A skin lesion imaged with a dermatoscope — 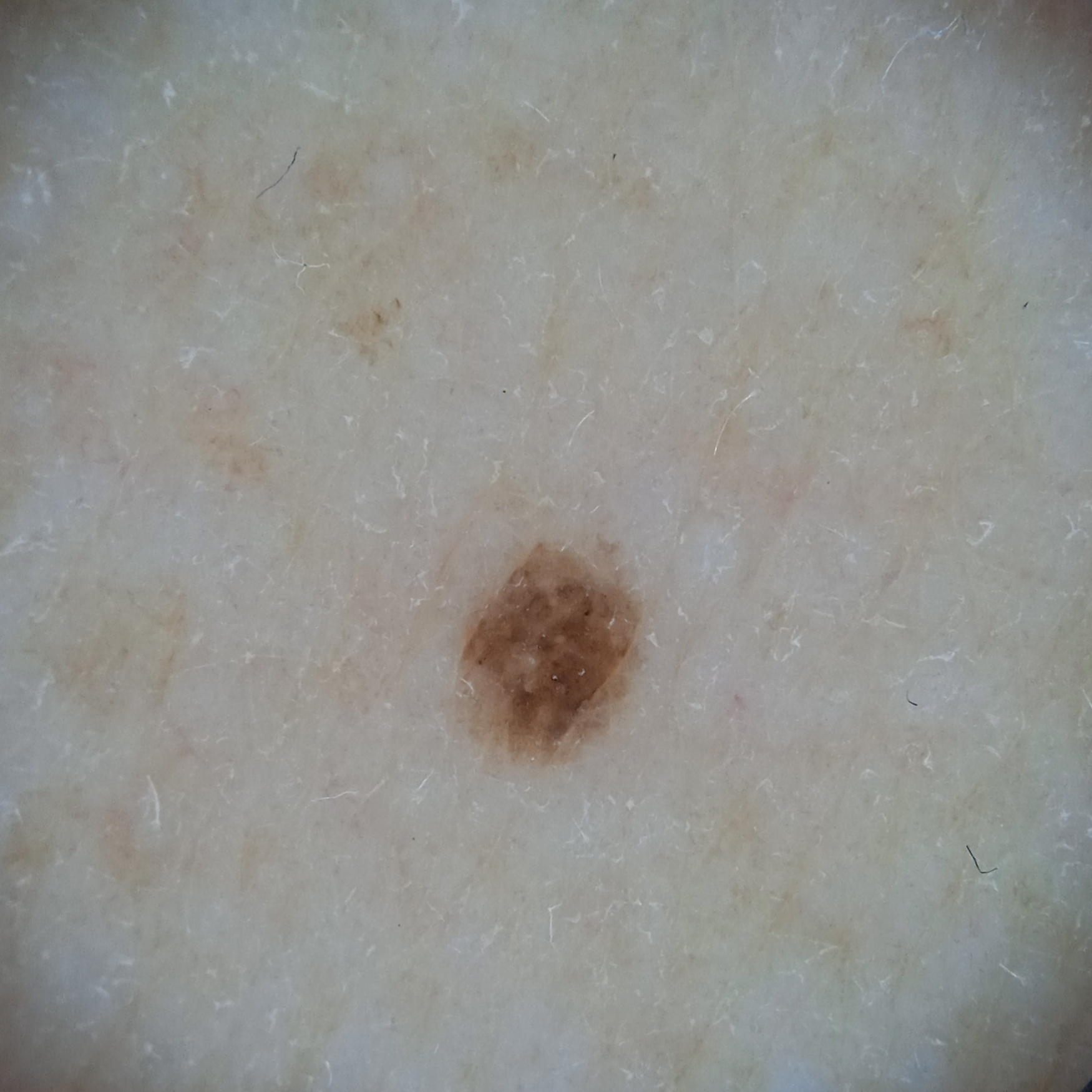The diagnostic impression was a melanocytic nevus.